The affected area is the arm · an image taken at an angle · the contributor is a female aged 60–69.
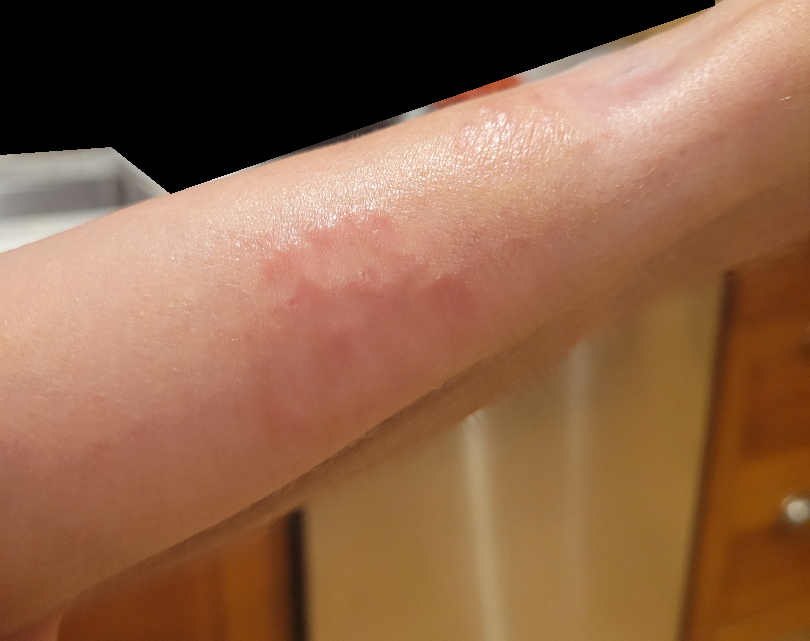Review: A single dermatologist reviewed the case: most likely Granuloma annulare; possibly Erythema annulare centrifugum; less probable is Cutaneous sarcoidosis.